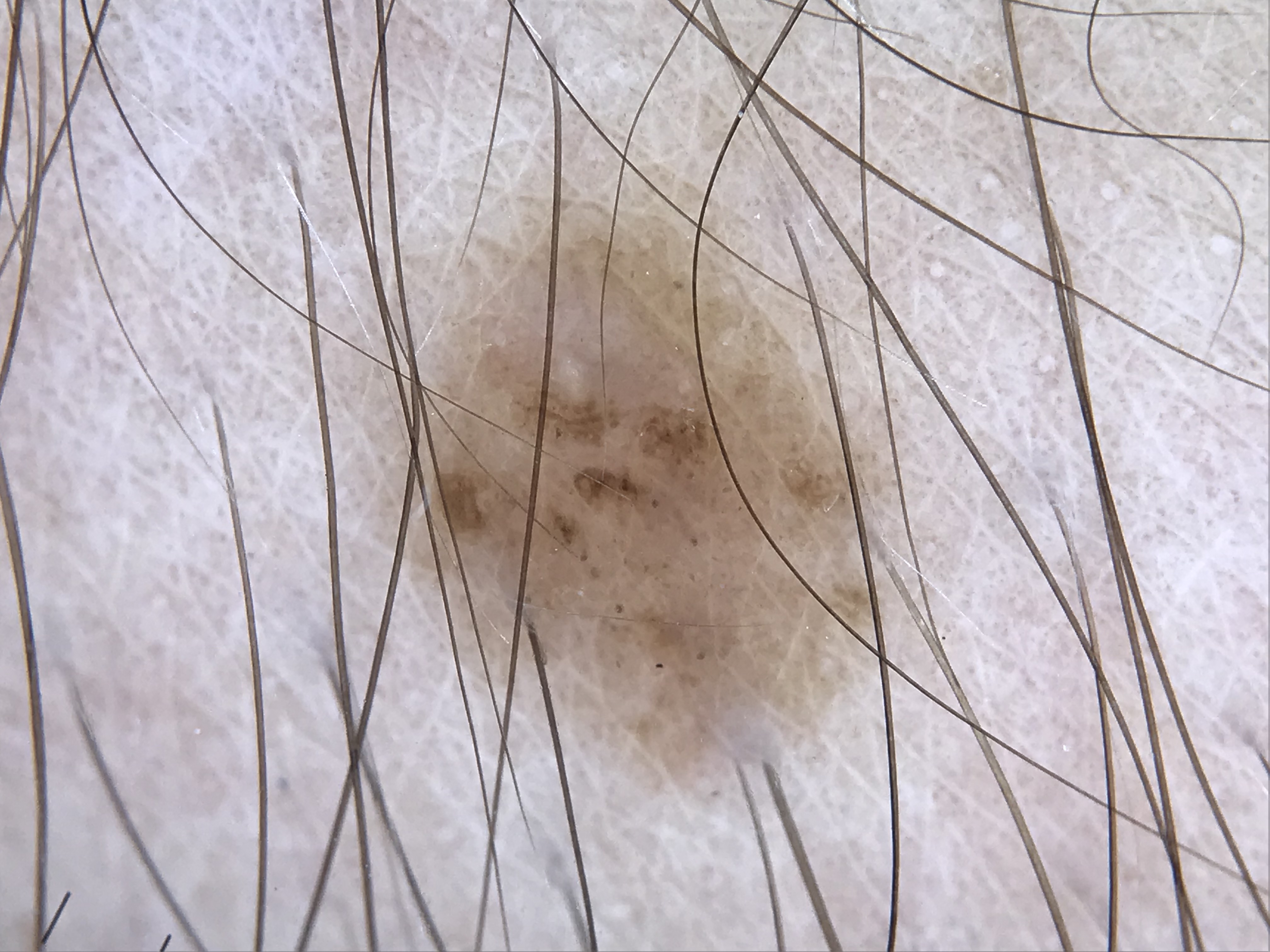Q: What kind of image is this?
A: dermatoscopy
Q: What is this lesion?
A: dysplastic junctional nevus (expert consensus)